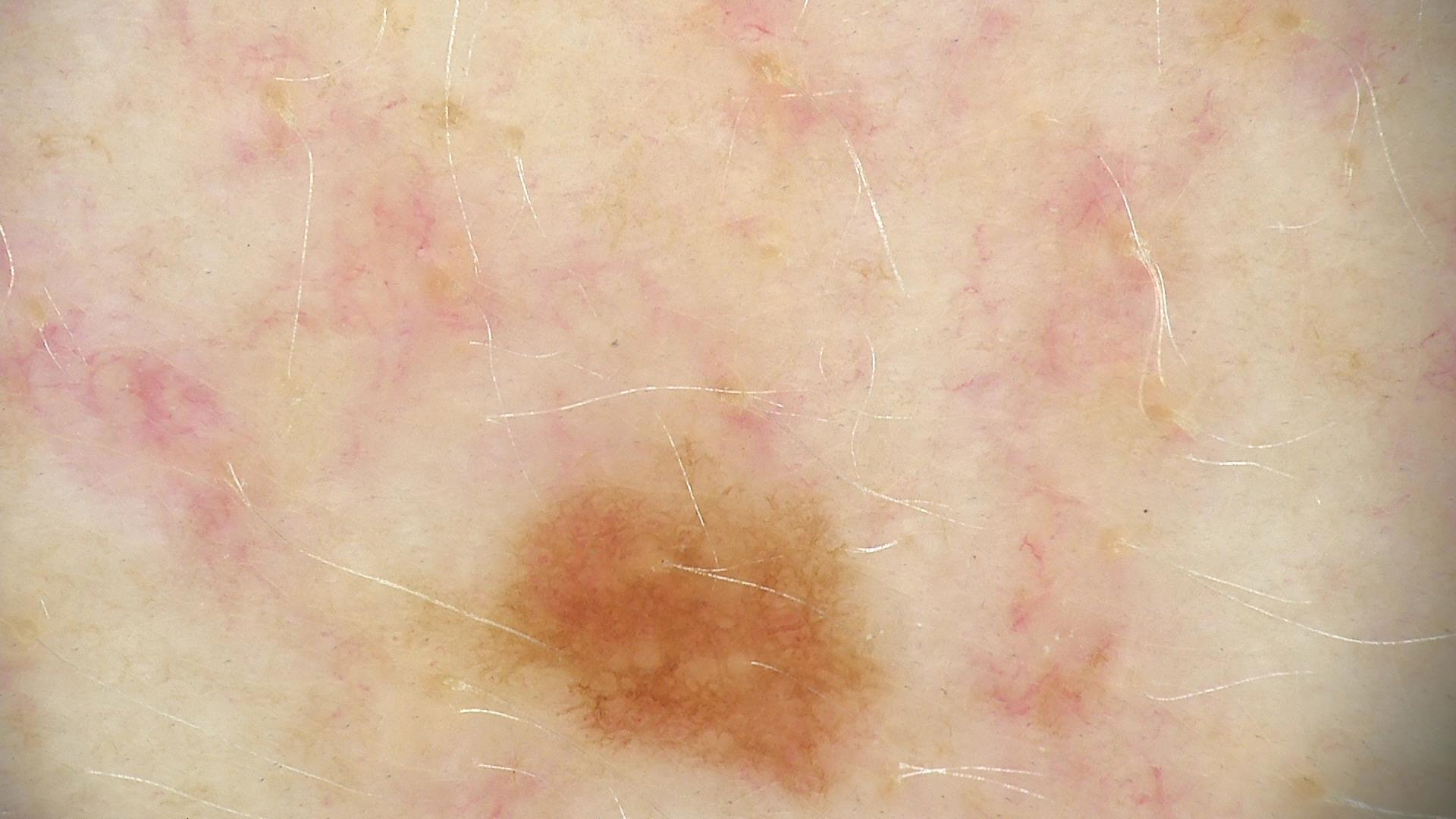The diagnostic label was a benign lesion — a dysplastic junctional nevus.